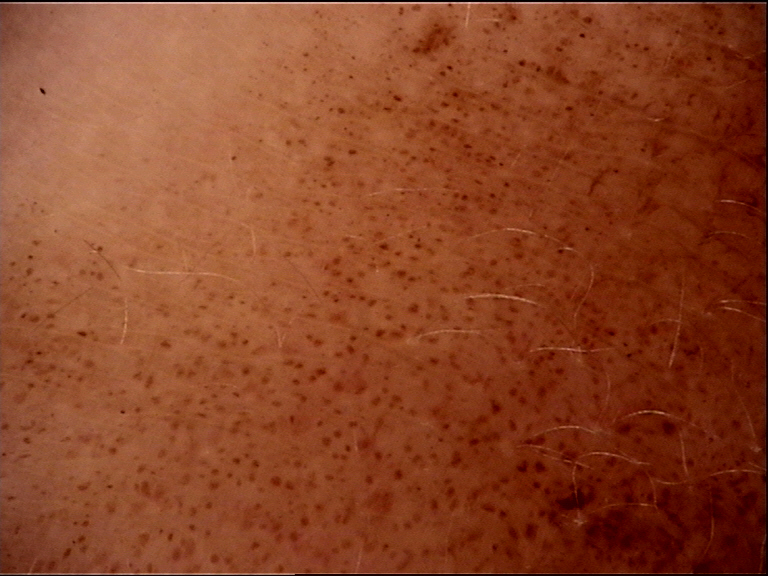image: dermoscopy
lesion_type:
  main_class: banal
  pattern: junctional
diagnosis:
  name: congenital junctional nevus
  code: cjb
  malignancy: benign
  super_class: melanocytic
  confirmation: expert consensus